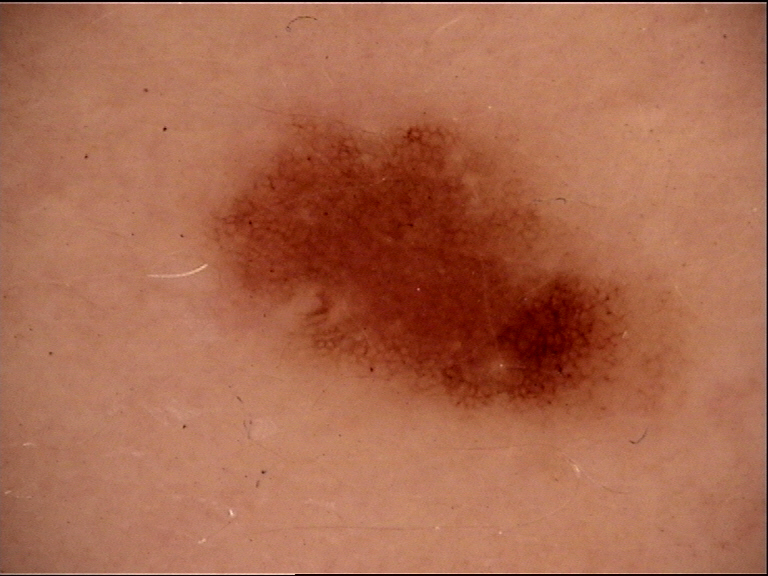<dermoscopy>
<diagnosis>
<name>dysplastic junctional nevus</name>
<code>jd</code>
<malignancy>benign</malignancy>
<super_class>melanocytic</super_class>
<confirmation>expert consensus</confirmation>
</diagnosis>
</dermoscopy>